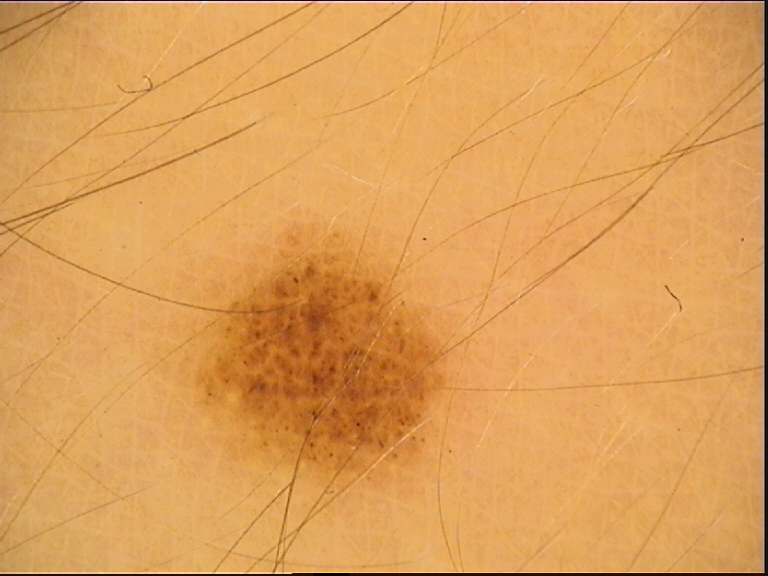diagnosis: junctional nevus (expert consensus).